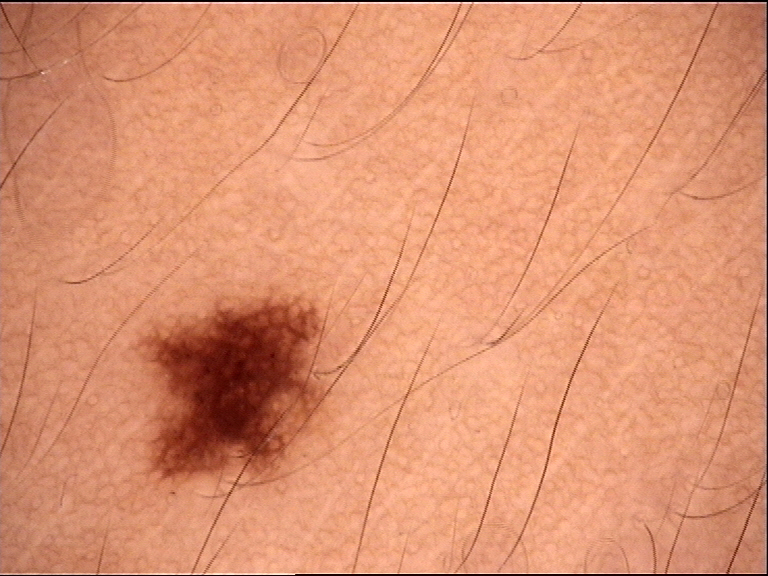Q: What is the imaging modality?
A: dermoscopy
Q: What was the diagnostic impression?
A: dysplastic junctional nevus (expert consensus)